Reported duration is less than one week, close-up view, texture is reported as flat, the affected area is the arm, the patient notes itching, self-categorized by the patient as a rash — 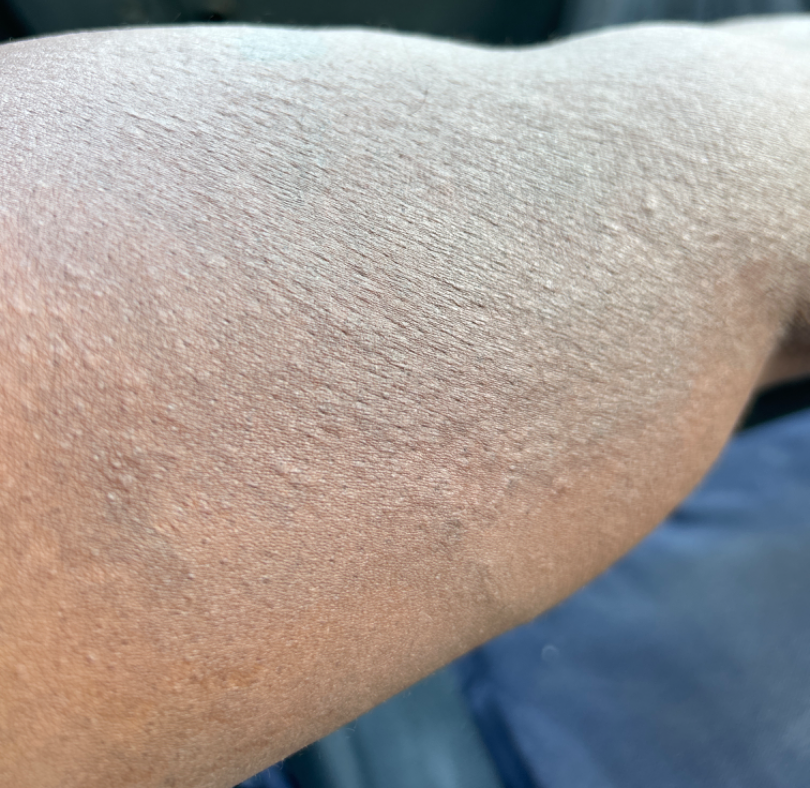Impression:
On photographic review by a dermatologist, in keeping with Eczema.